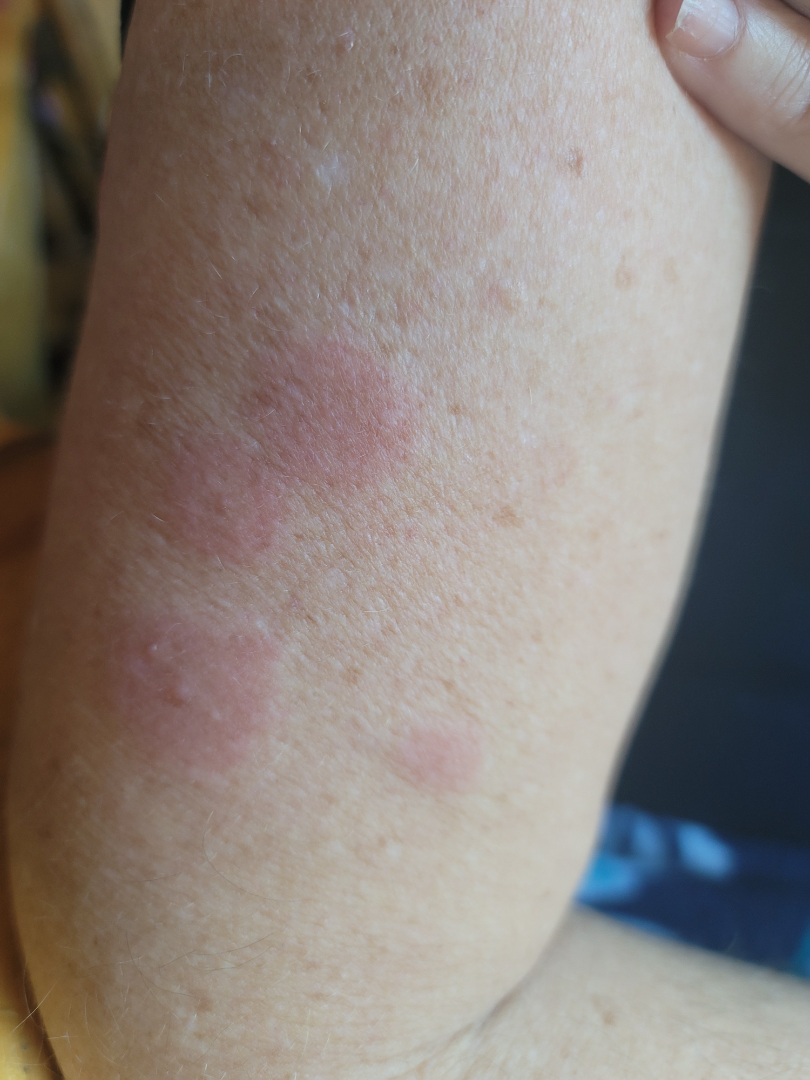Q: How long has this been present?
A: about one day
Q: How does the lesion feel?
A: raised or bumpy
Q: What is the framing?
A: close-up
Q: What is the patient's skin tone?
A: Fitzpatrick III; human graders estimated Monk Skin Tone 3 (US pool) or 2 (India pool)
Q: Constitutional symptoms?
A: none reported
Q: What is the affected area?
A: back of the hand, arm and head or neck
Q: What is the differential diagnosis?
A: the reviewer's impression was Acute dermatitis, NOS